A dermatoscopic image of a skin lesion.
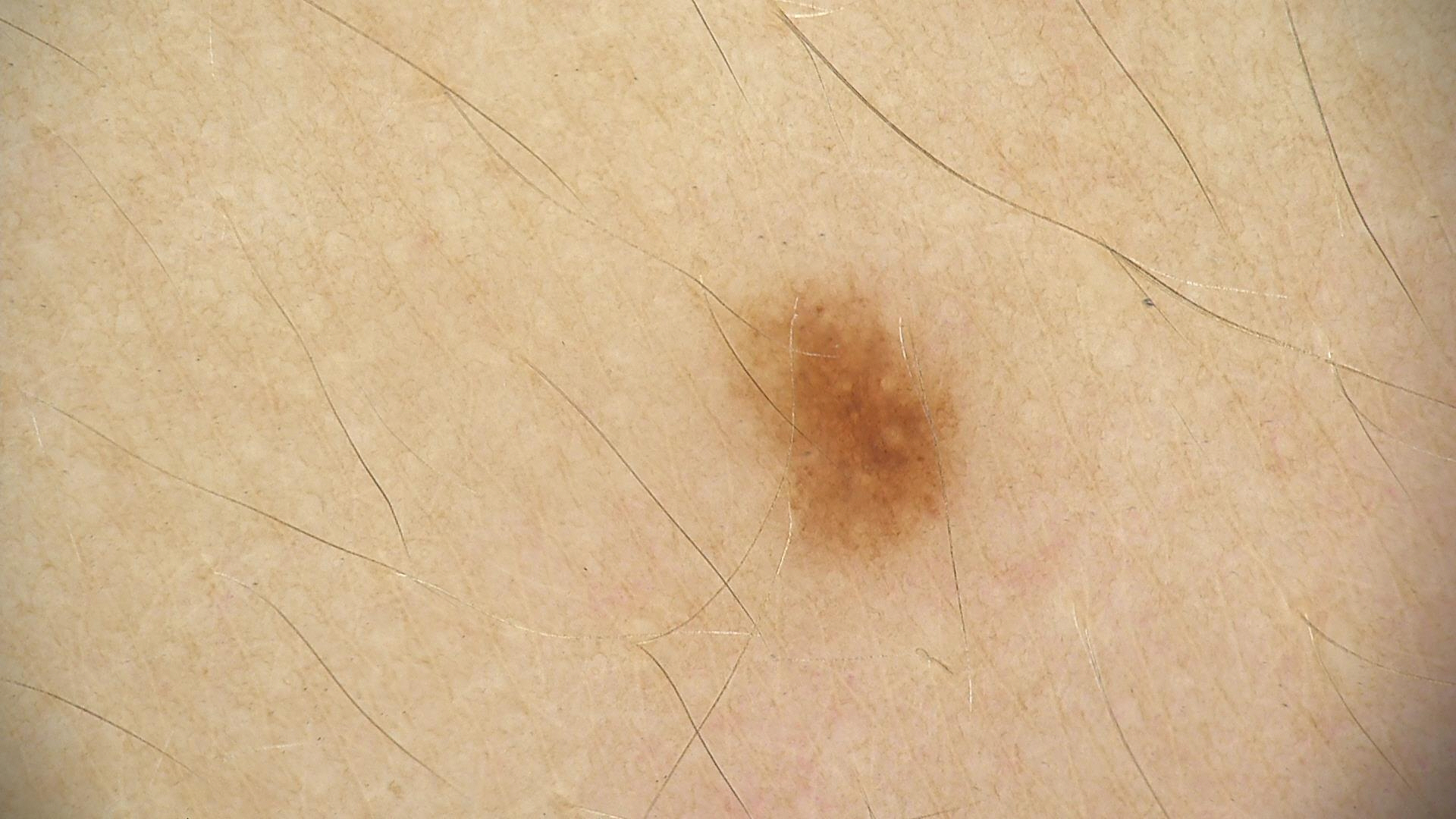lesion type = banal; diagnosis = junctional nevus (expert consensus).